A clinical close-up photograph of a skin lesion; a subject age 67 — 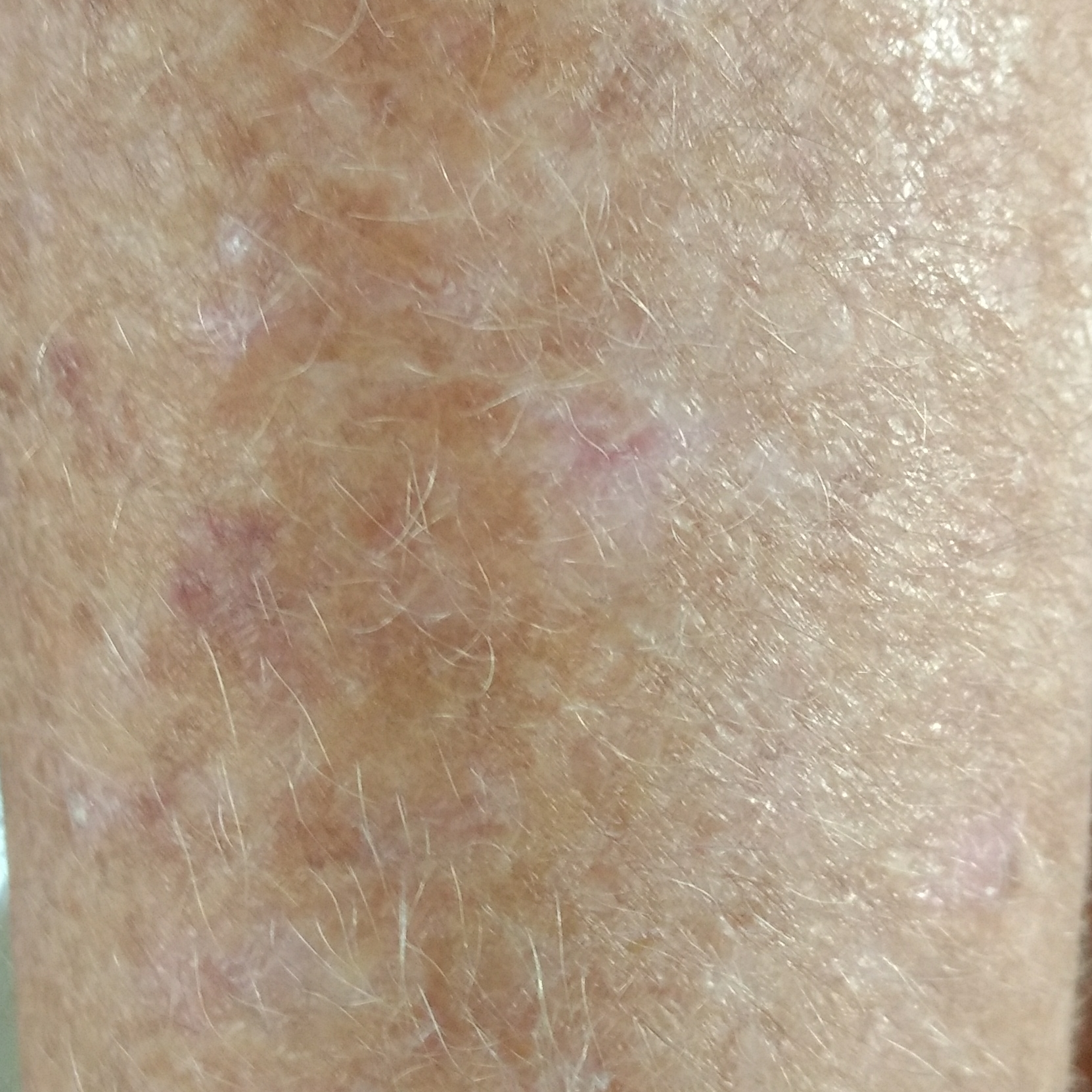Q: What is the anatomic site?
A: a forearm
Q: Any reported symptoms?
A: itching / no change in appearance, no pain
Q: What is the diagnosis?
A: actinic keratosis (clinical consensus)